A female patient aged 32; a moderate number of moles by the patient's own estimate; the patient says their skin reddens with sun exposure; acquired for a research image collection, with no referral diagnosis: 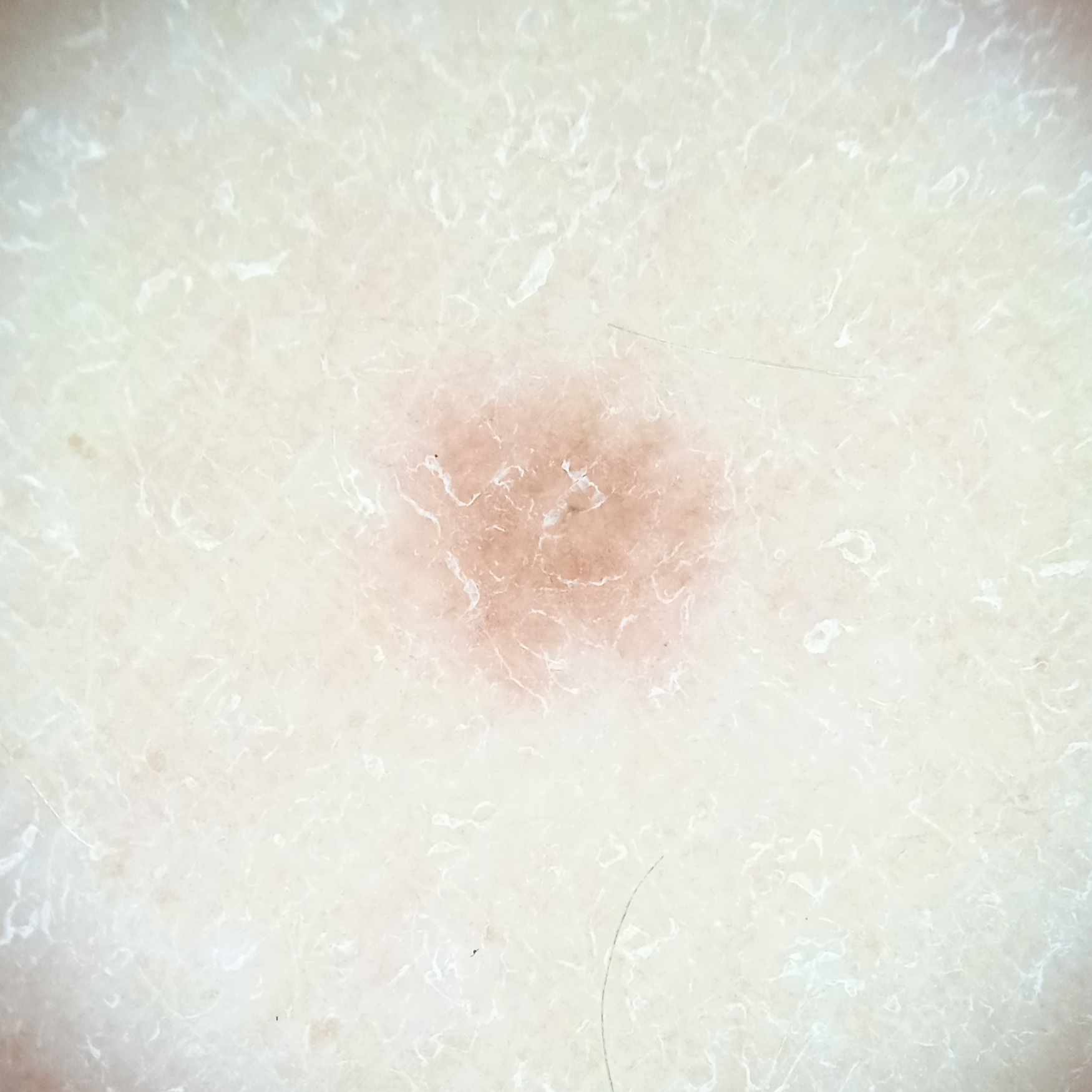Findings:
– size — 4.1 mm
– diagnosis — melanocytic nevus (dermatologist consensus)